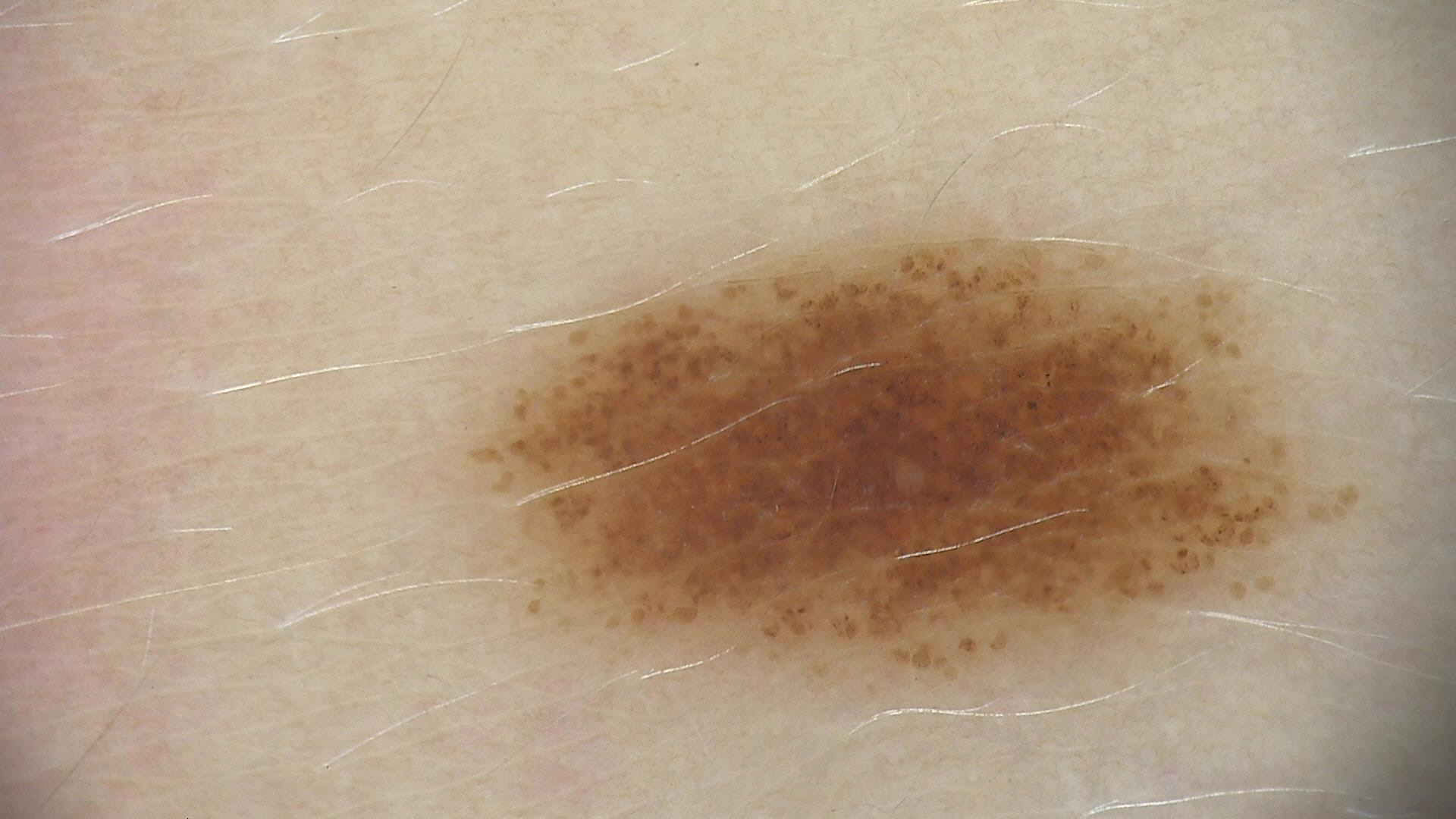Classified as a dysplastic junctional nevus.